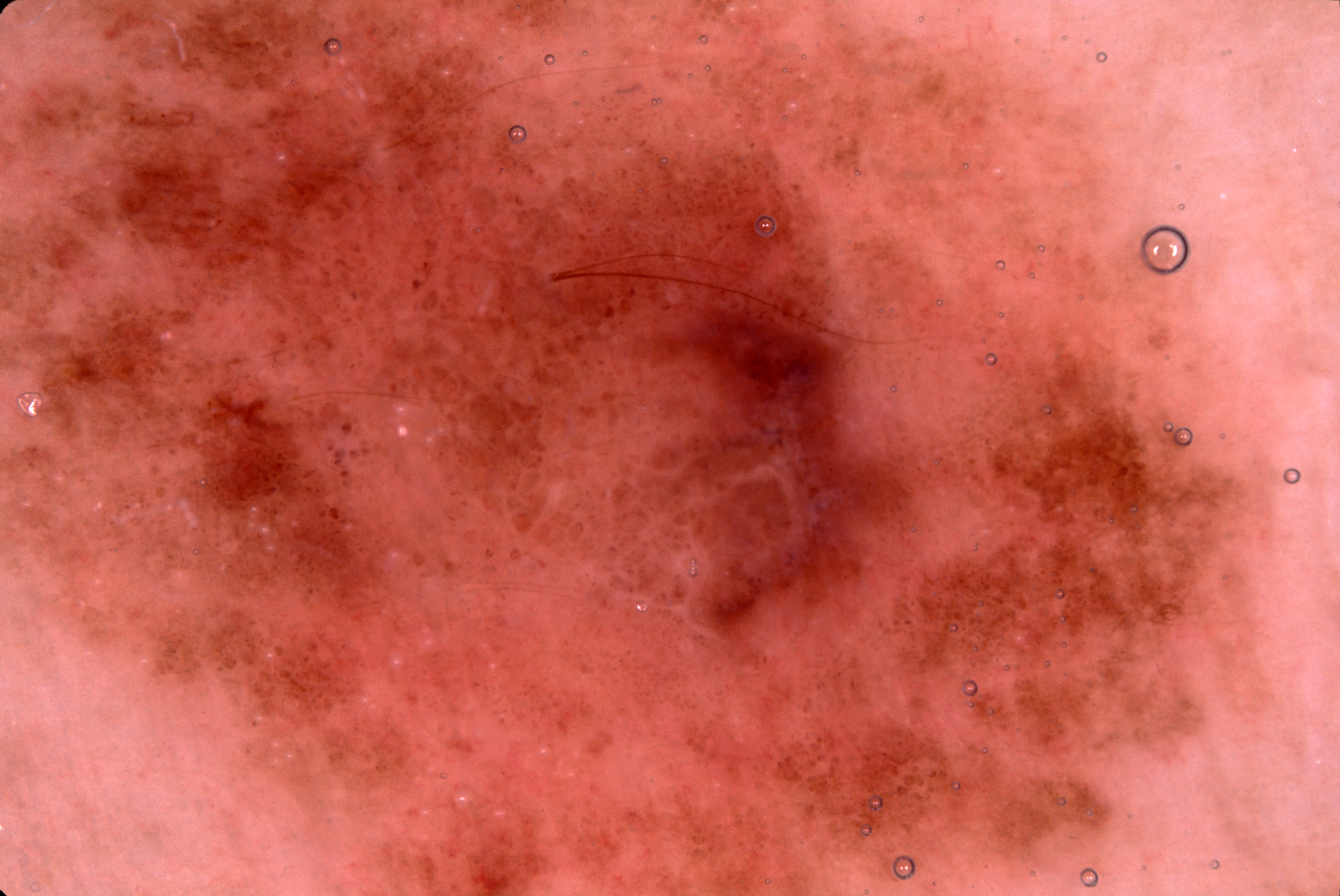subject = female, approximately 40 years of age; image type = dermoscopy; dermoscopic features = milia-like cysts and negative network; lesion location = spans the dermoscopic field; diagnosis = a melanocytic nevus.